The contributor reports the lesion is raised or bumpy. The contributor reports the condition has been present for about one day. The contributor reports itching. The patient considered this a rash. An image taken at an angle. The affected area is the back of the hand.
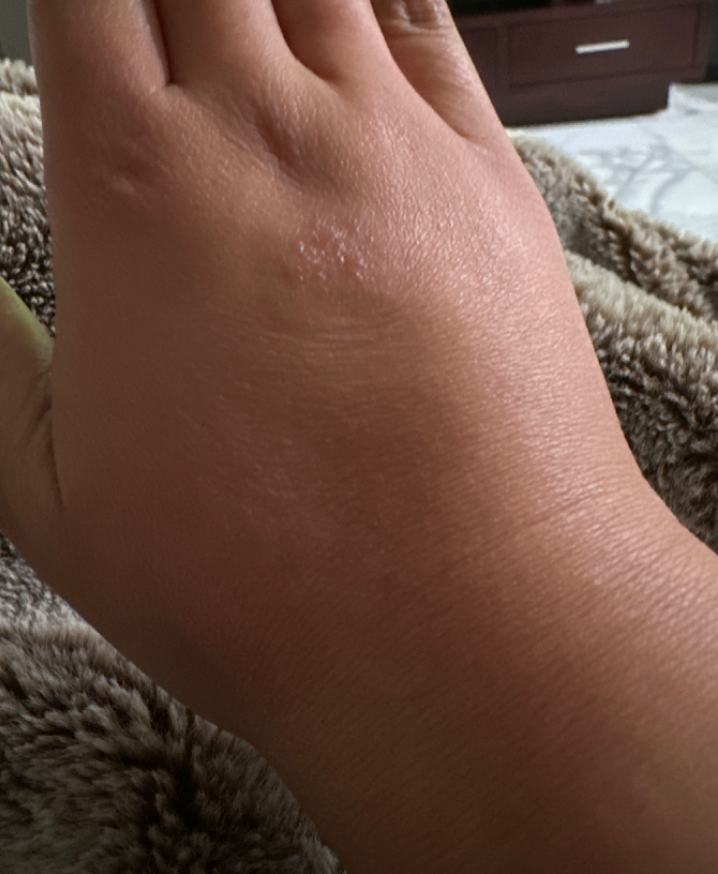| key | value |
|---|---|
| assessment | not assessable |